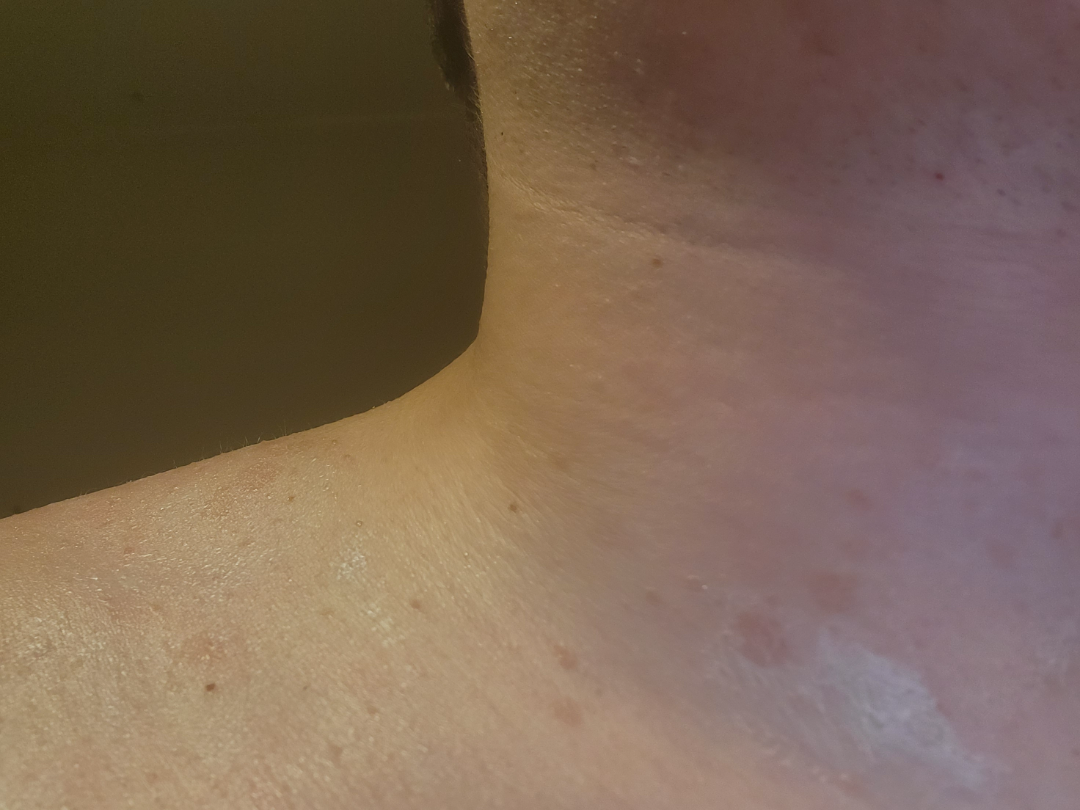The case was difficult to assess from the available photograph. The patient indicates associated joint pain. The lesion is associated with itching and bothersome appearance. Self-categorized by the patient as a rash. The lesion is described as flat and raised or bumpy. Fitzpatrick III; lay graders estimated MST 2 or 4 (two reviewer pools disagreed). The patient is 18–29, male. The patient indicates the condition has been present for one to four weeks. The affected area is the front of the torso and head or neck. A close-up photograph.